The lesion is associated with burning, pain and itching. The lesion is described as rough or flaky and raised or bumpy. This image was taken at an angle. The palm is involved. The condition has been present for about one day: 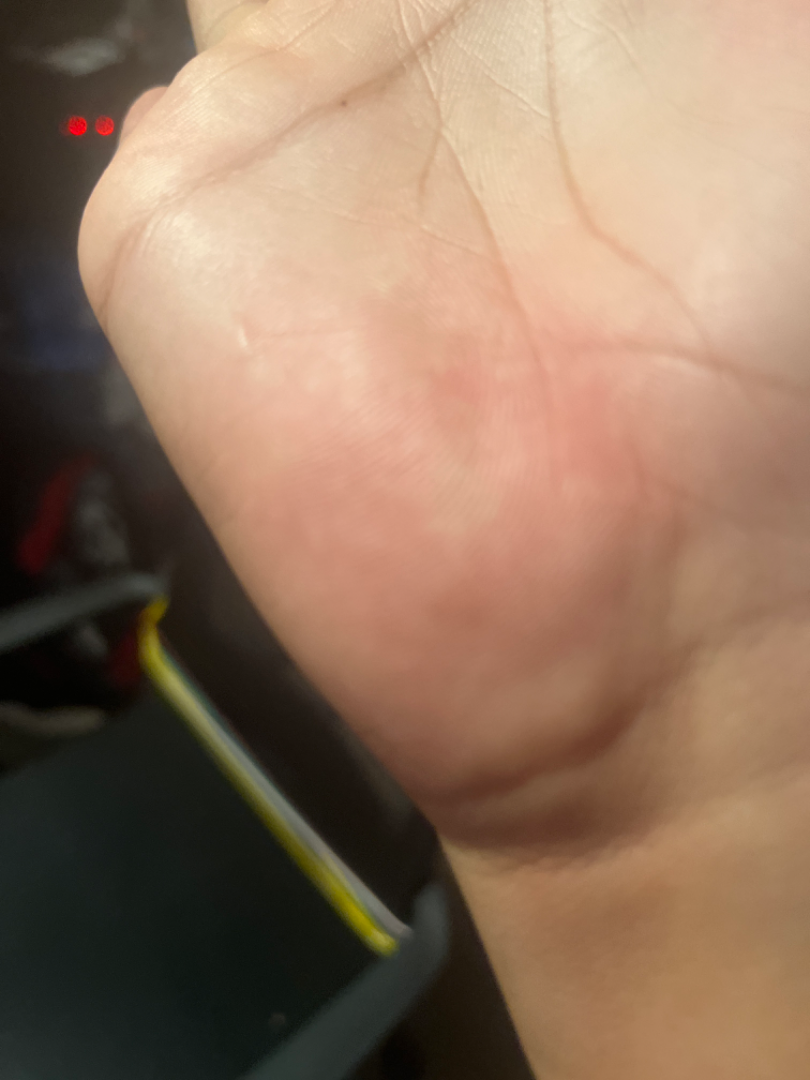Findings:
No differential diagnosis could be assigned on photographic review.